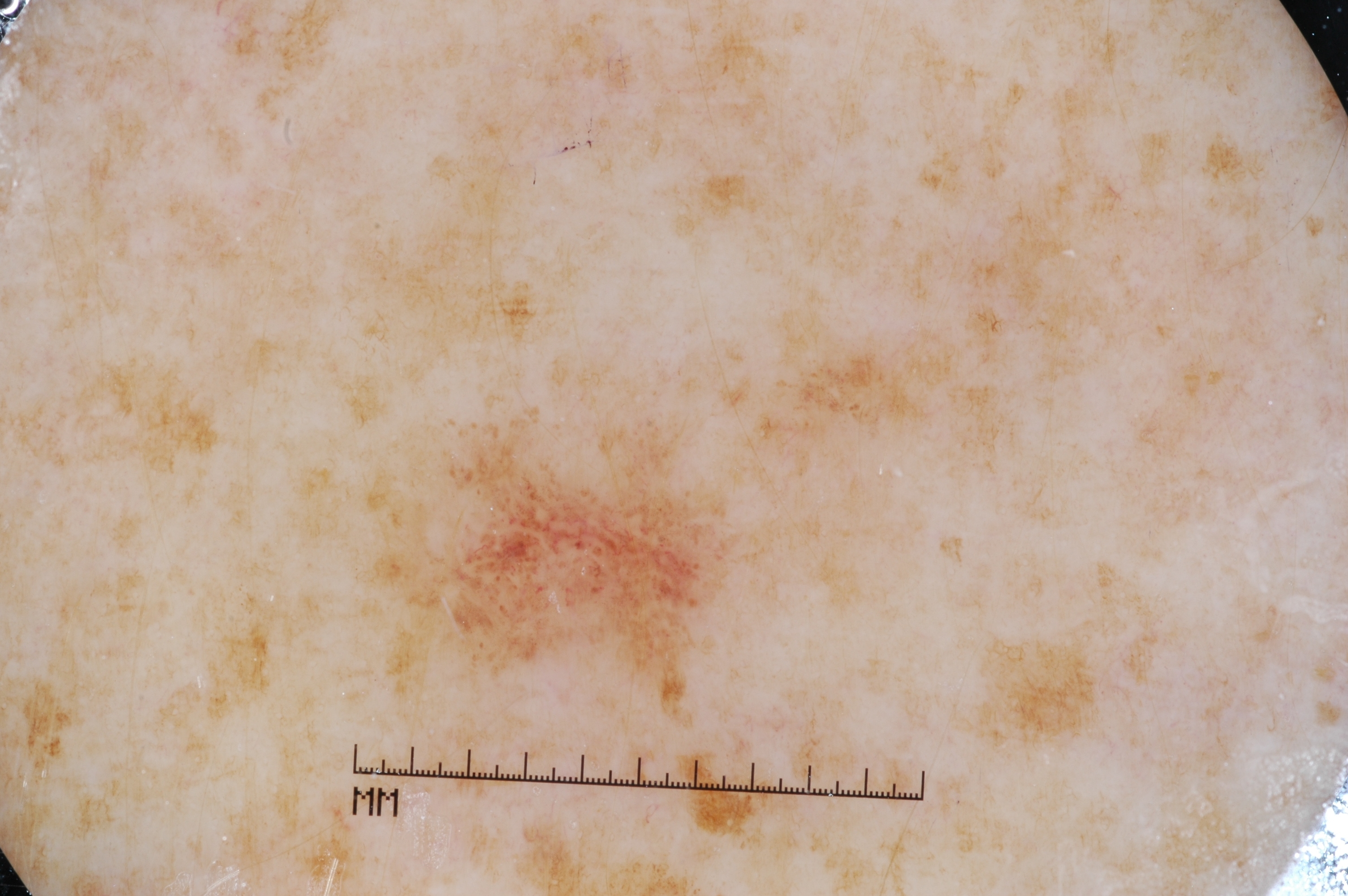Q: Patient demographics?
A: female, aged around 40
Q: How was this image acquired?
A: dermoscopic image
Q: How large is the lesion within the image?
A: ~4% of the field
Q: What does dermoscopy show?
A: negative network
Q: What is the lesion's bounding box?
A: 390, 441, 726, 672
Q: What is this lesion?
A: a melanocytic nevus